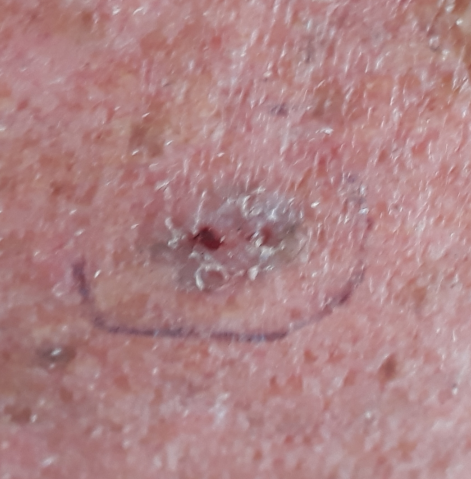Pathology: On biopsy, the diagnosis was a basal cell carcinoma.